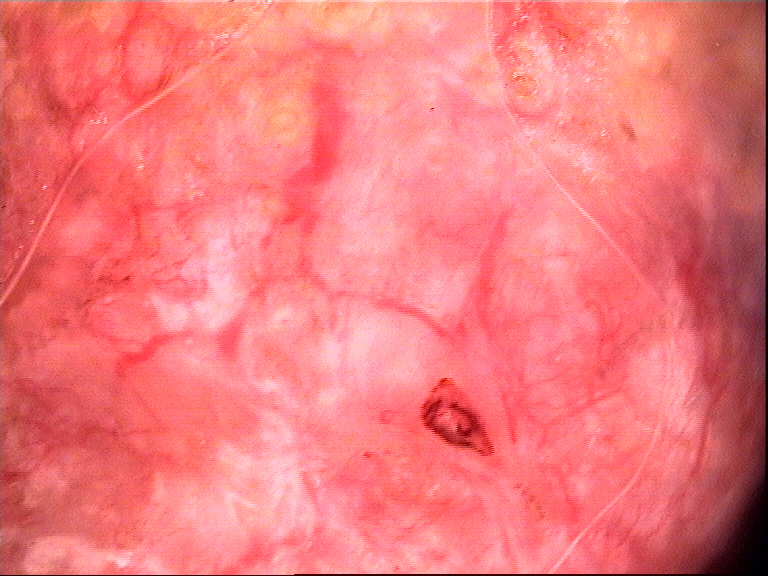Q: What is the imaging modality?
A: dermoscopy
Q: What did the workup show?
A: basal cell carcinoma (biopsy-proven)